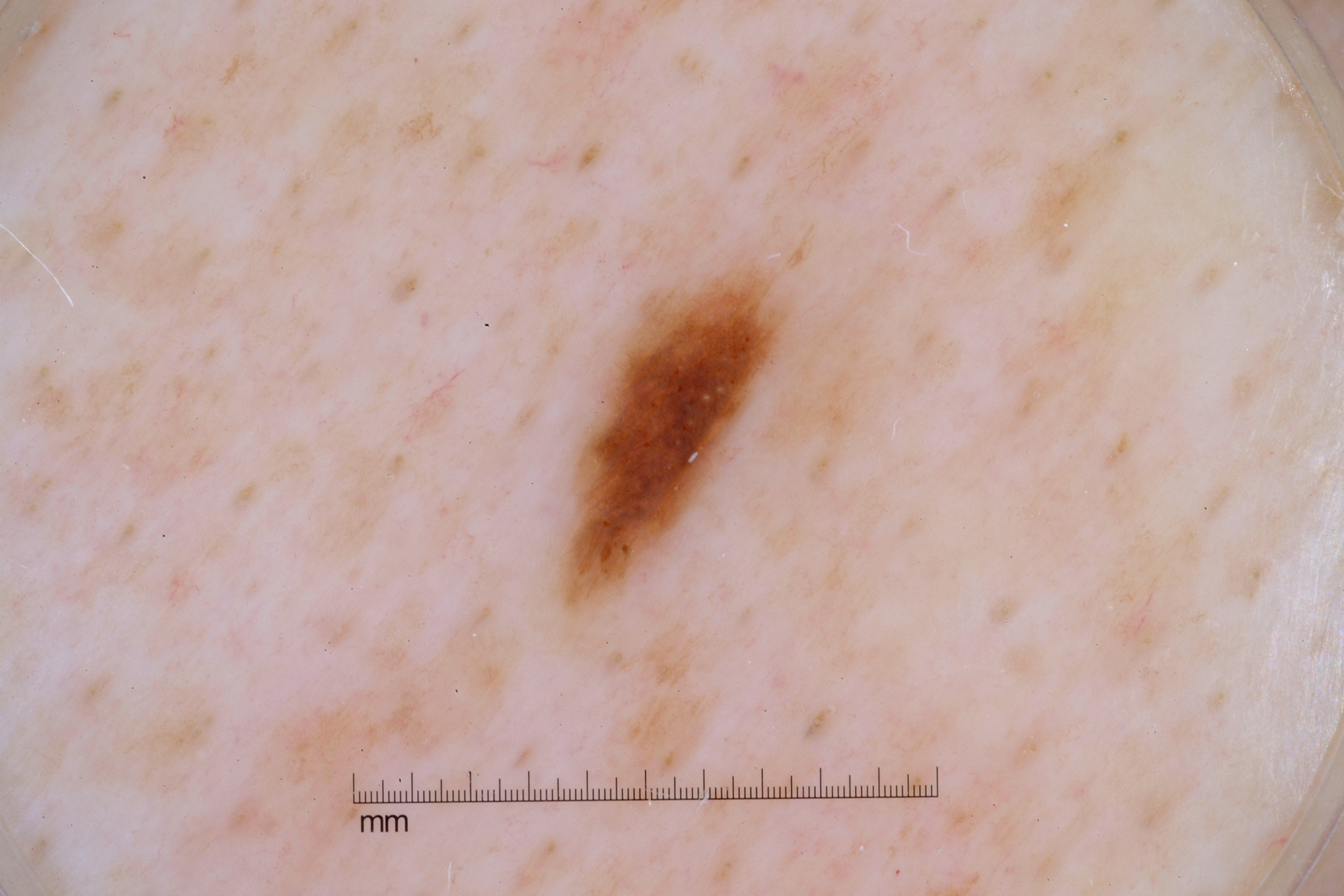Q: What kind of image is this?
A: dermatoscopic image of a skin lesion
Q: What are the patient's age and sex?
A: male, approximately 60 years of age
Q: Where is the lesion in the image?
A: <bbox>555, 258, 796, 617</bbox>
Q: What does dermoscopy show?
A: milia-like cysts and pigment network; absent: negative network and streaks
Q: How large is the lesion within the image?
A: ~4% of the field
Q: What did the assessment conclude?
A: a melanocytic nevus